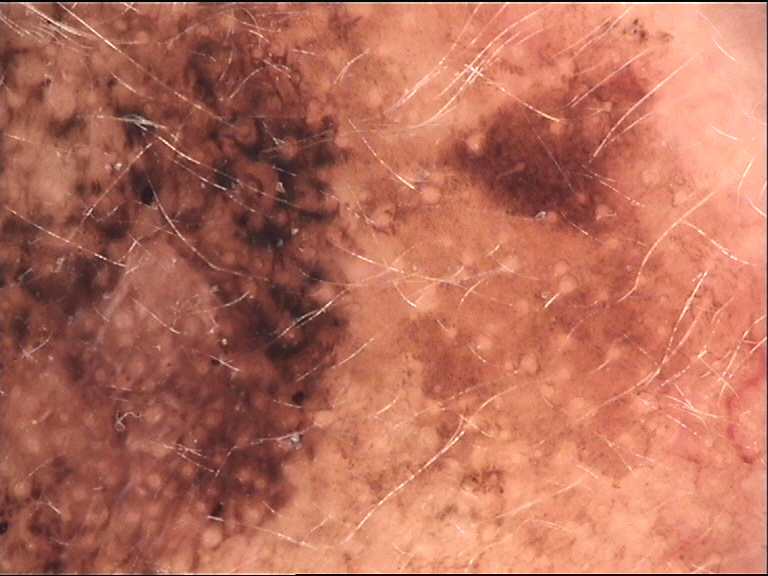image type=dermoscopy
label=lentigo maligna (biopsy-proven)